The back of the torso and head or neck are involved; close-up view; male subject, age 18–29: 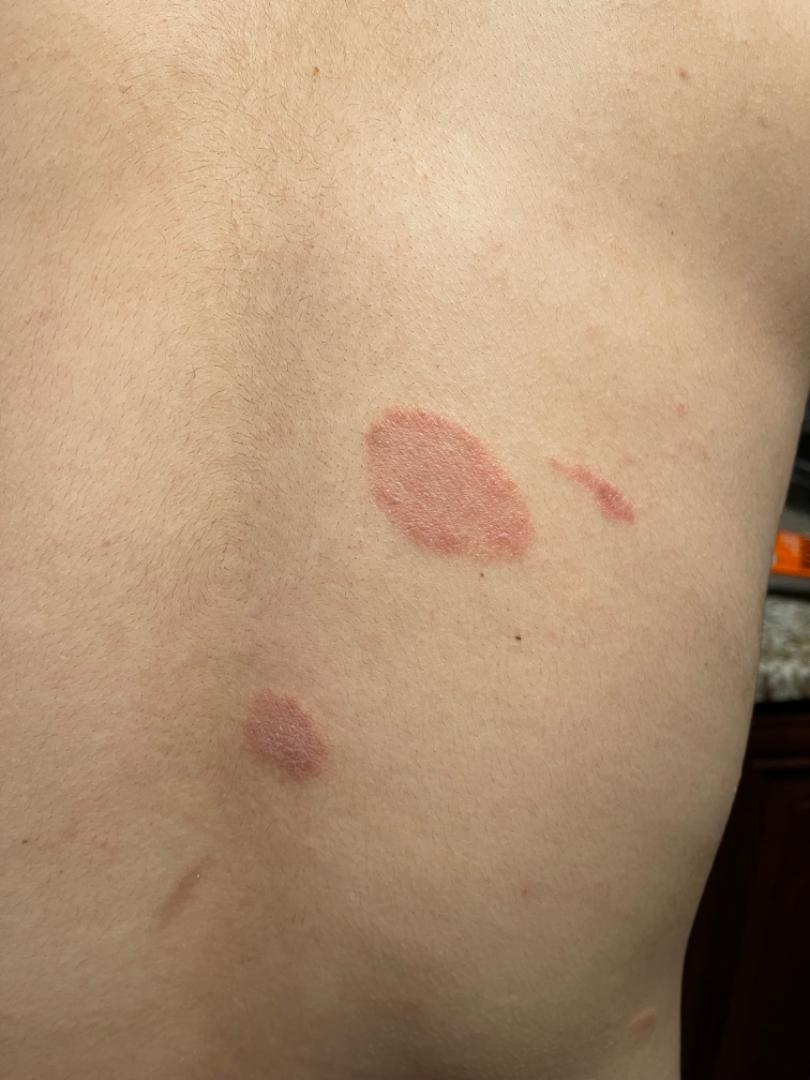differential:
  tied_lead:
    - Psoriasis
    - Eczema
    - Pityriasis rosea